A dermoscopic image of a skin lesion.
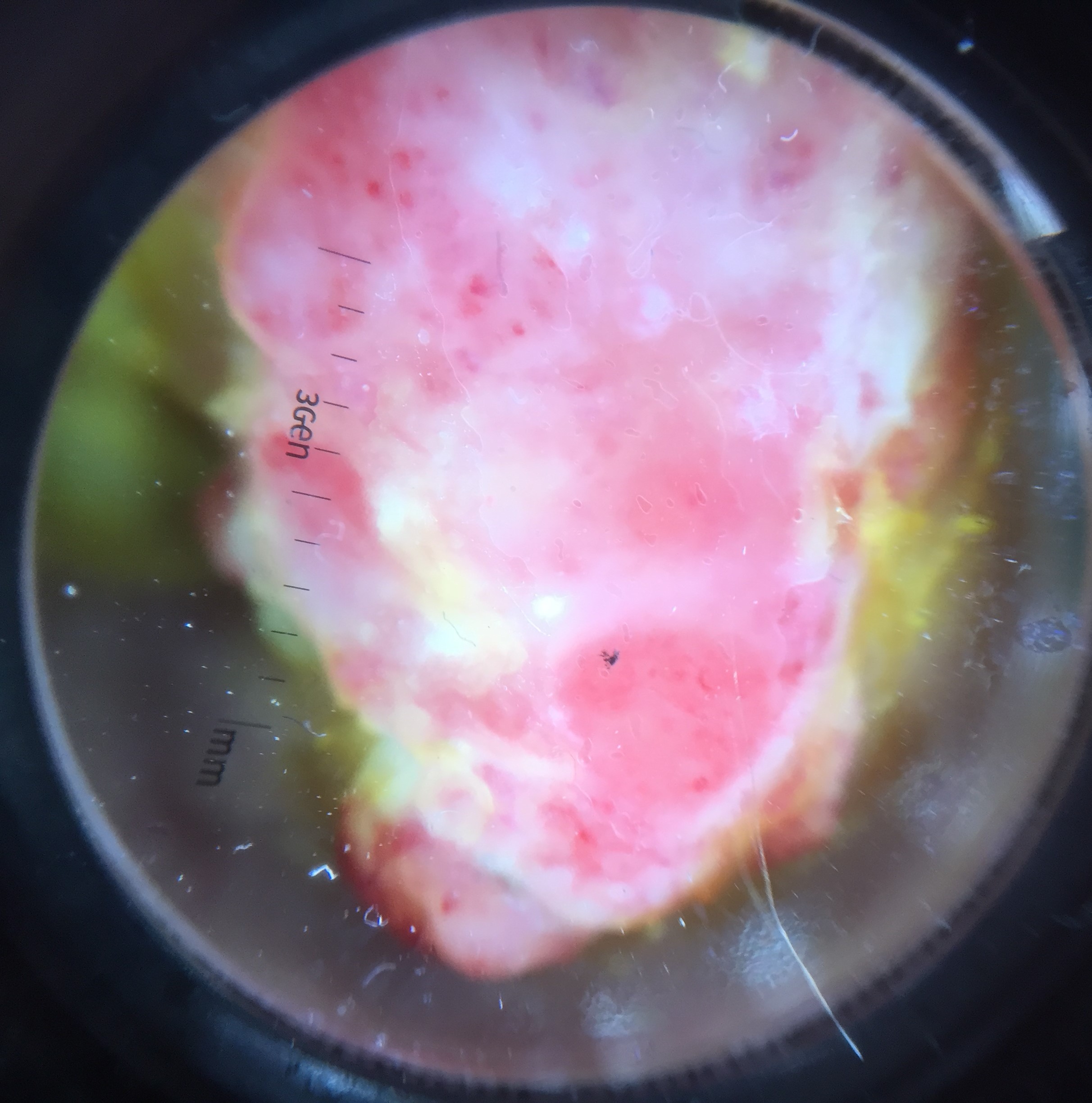diagnosis: acral nodular melanoma (biopsy-proven).